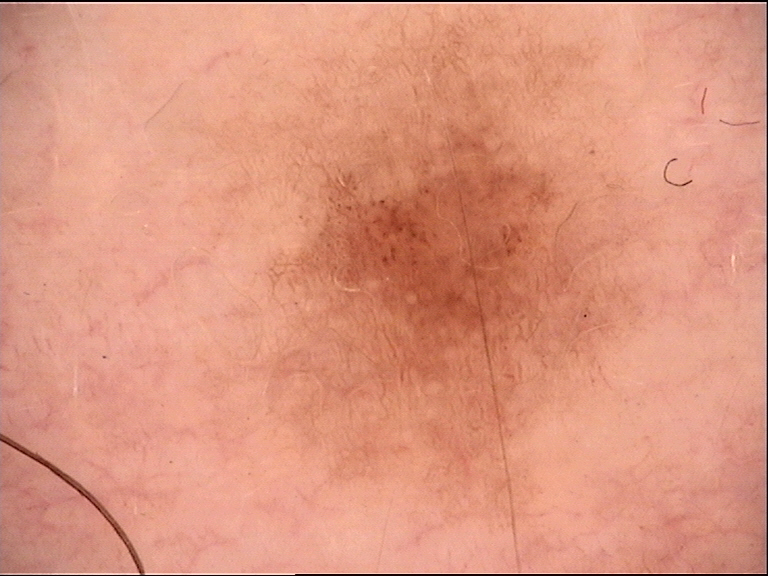class: dysplastic junctional nevus (expert consensus)